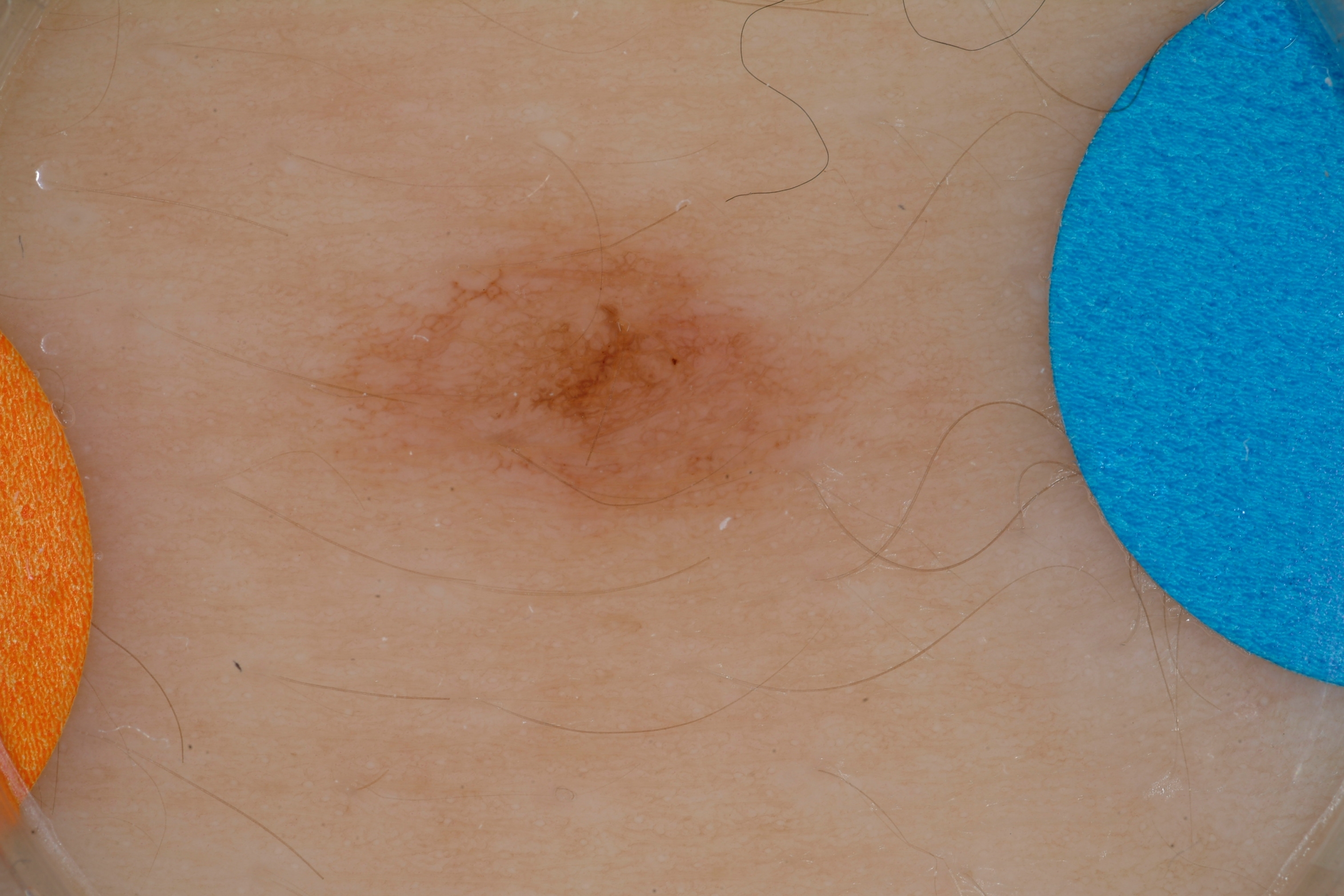A dermoscopic image of a skin lesion.
A male patient approximately 15 years of age.
The lesion covers approximately 13% of the dermoscopic field.
Dermoscopy demonstrates pigment network.
The lesion is located at x1=306, y1=203, x2=887, y2=544.
Expert review diagnosed this as a melanocytic nevus, a benign skin lesion.